Contact-polarized dermoscopy of a skin lesion; a female subject aged 68-72: 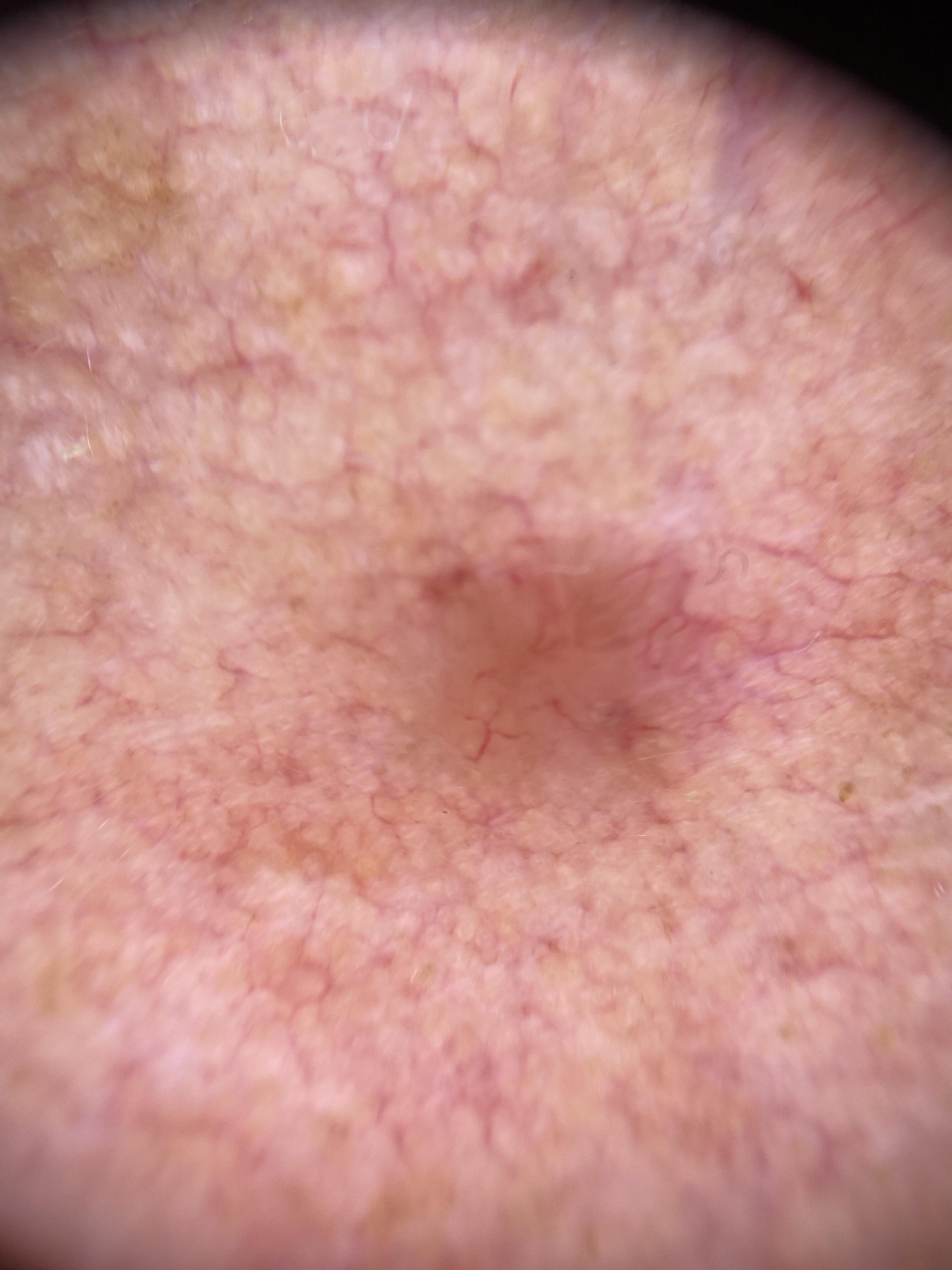Clinical context: The lesion is on the head or neck. Conclusion: Confirmed on histopathology as a basal cell carcinoma.